Texture is reported as raised or bumpy · the contributor is 60–69, female · the patient reported no systemic symptoms · located on the leg · the photograph was taken at an angle · the patient notes the condition has been present for less than one week · self-categorized by the patient as a rash: 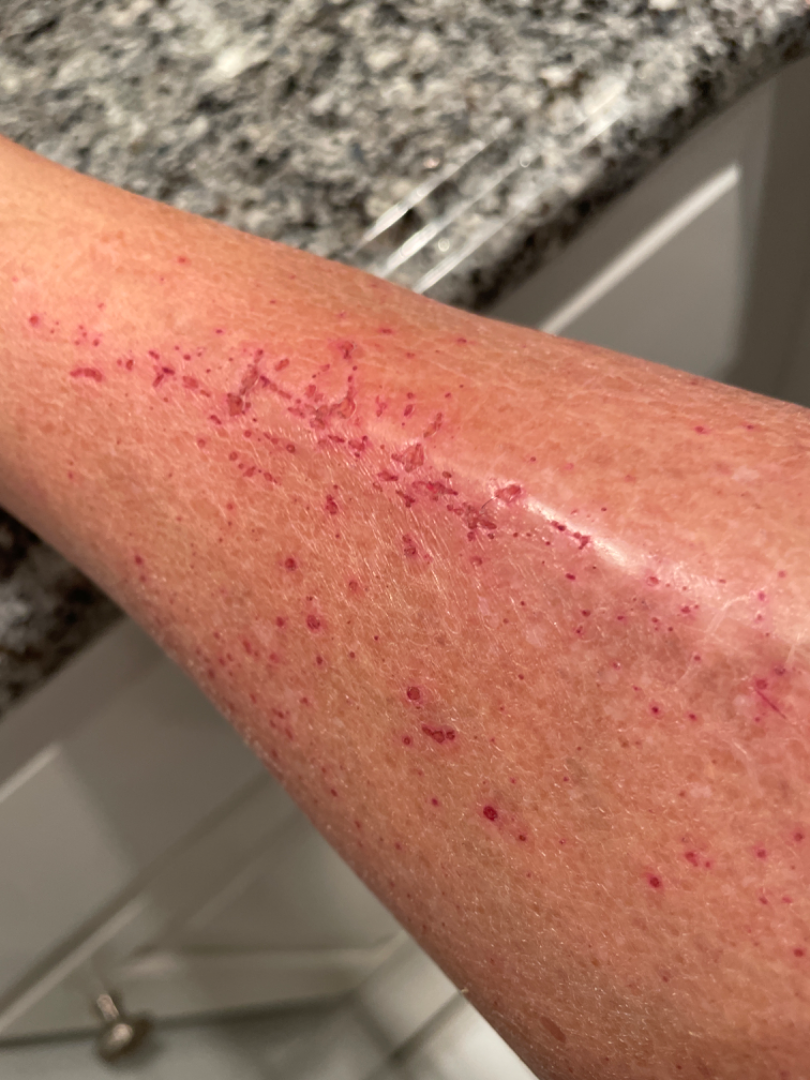Eczema (67%); Xerosis (33%).